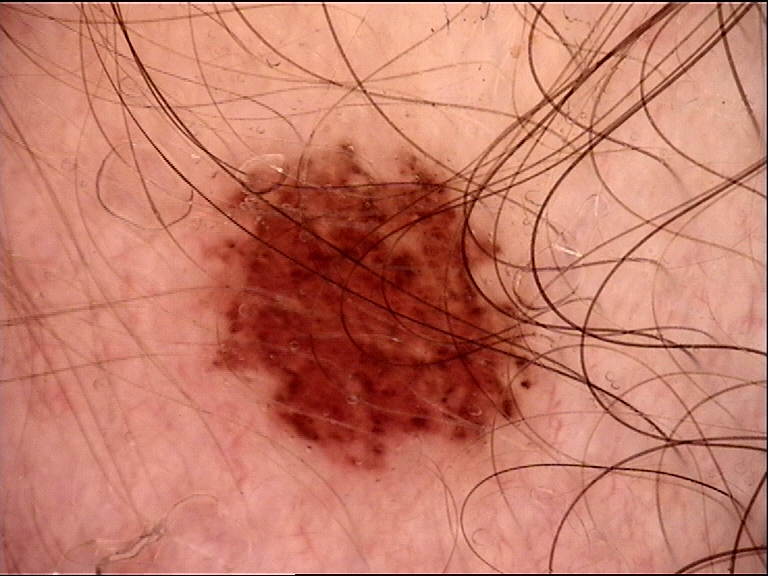The diagnostic label was a dysplastic junctional nevus.